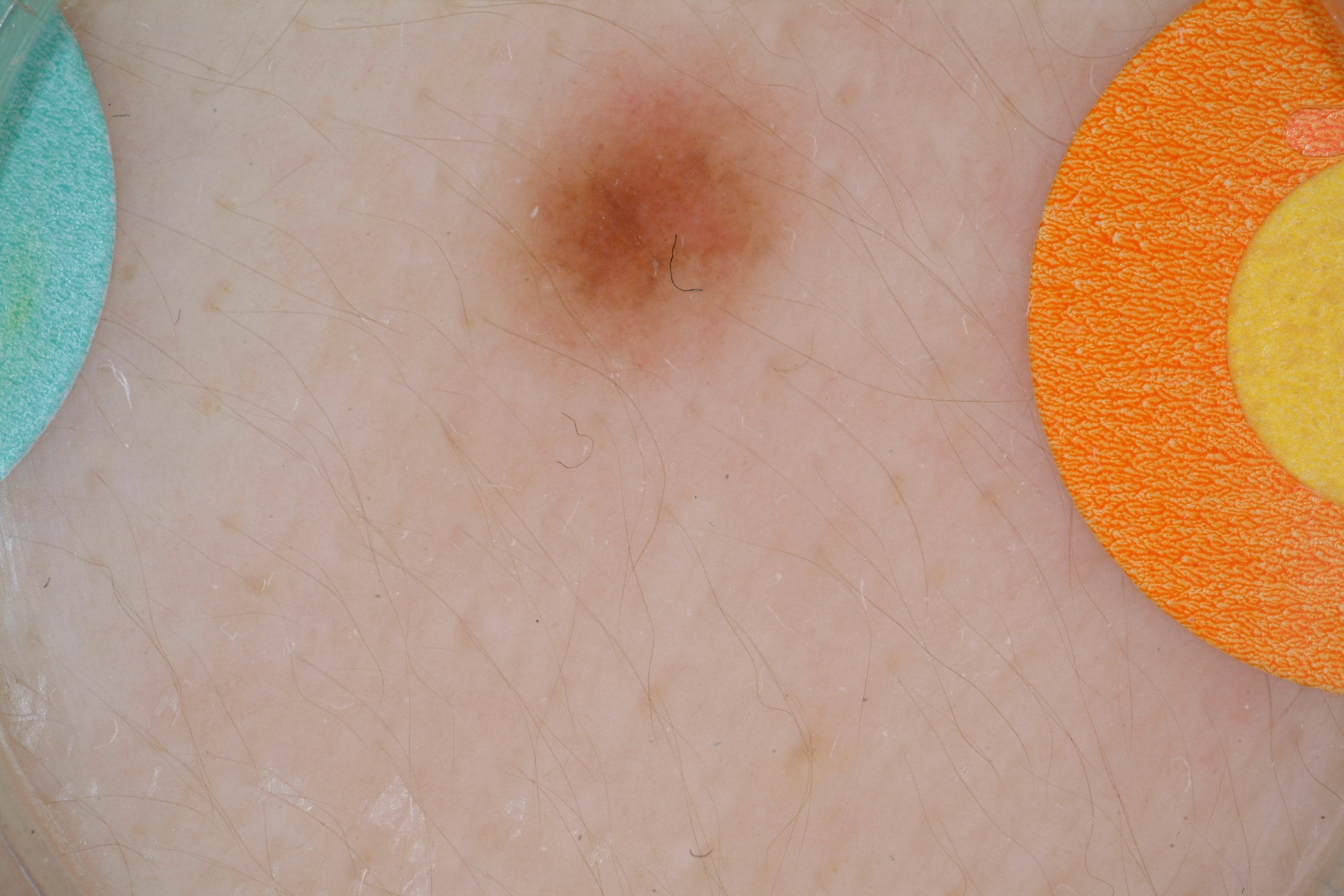Image and clinical context: A female subject, approximately 15 years of age. A dermatoscopic image of a skin lesion. On dermoscopy, the lesion shows no pigment network, milia-like cysts, globules, negative network, or streaks. The lesion takes up a moderate portion of the field. With coordinates (x1, y1, x2, y2), the lesion's extent is bbox=[466, 19, 825, 398]. Conclusion: Consistent with a melanocytic nevus, a benign skin lesion.